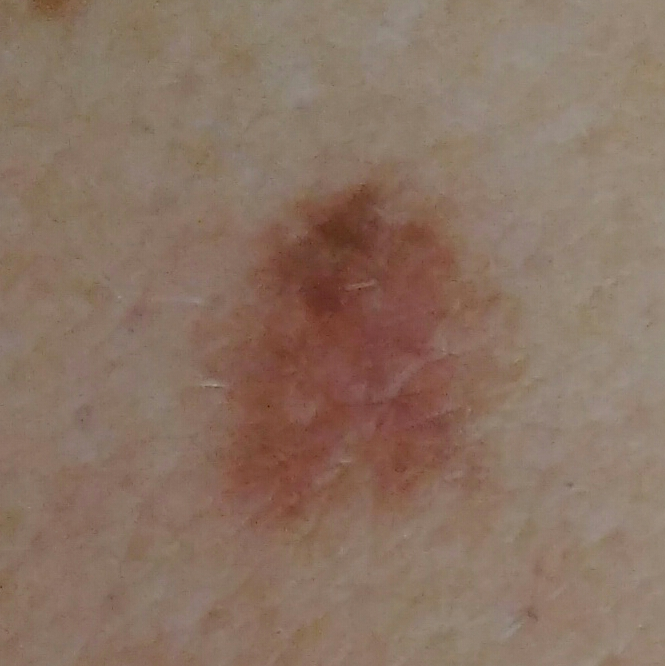Case summary:
Fitzpatrick IV. A female patient in their 60s. The chart notes prior malignancy (patient or family) and prior skin cancer (patient or family). A smartphone photograph of a skin lesion. The lesion involves the back. The lesion is roughly 5 by 4 mm. The patient reports that the lesion does not itch.
Conclusion:
The biopsy diagnosis was a benign lesion — a nevus.